The photograph was taken at a distance; the patient notes the condition has been present for three to twelve months; male contributor, age 40–49; the affected area is the top or side of the foot and leg; the lesion is described as flat; self-categorized by the patient as a growth or mole:
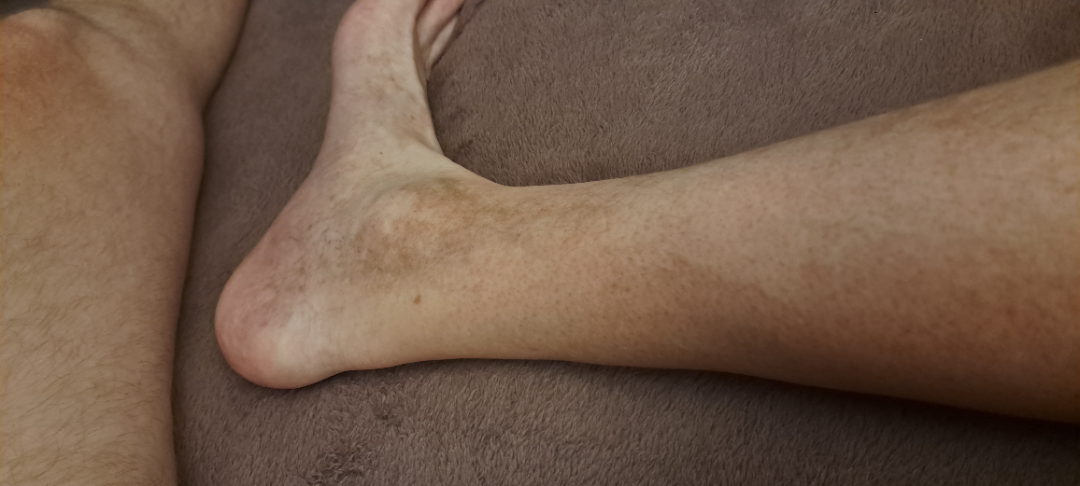Findings:
• dermatologist impression — Stasis Dermatitis, Pigmented purpuric eruption and Hemosiderin pigmentation of skin due to venous insufficiency were each considered, in no particular order